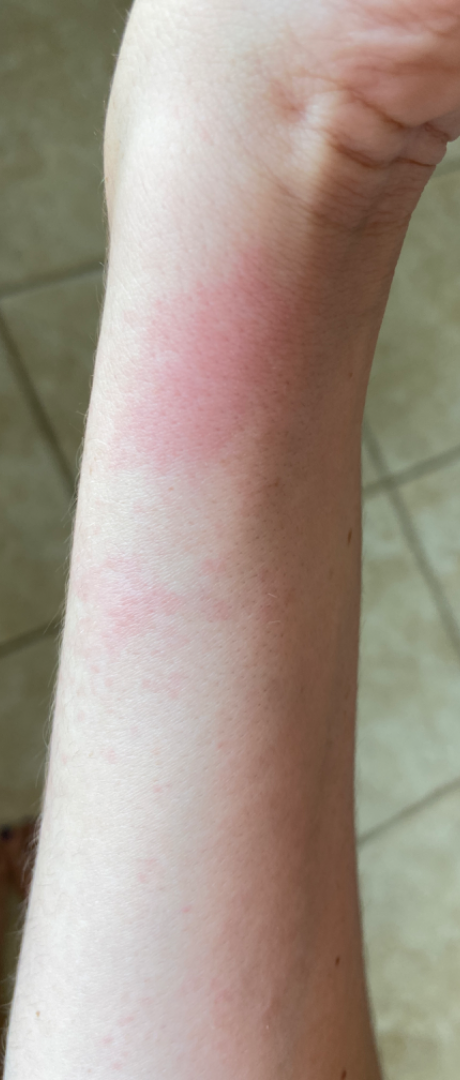| feature | finding |
|---|---|
| assessment | indeterminate |